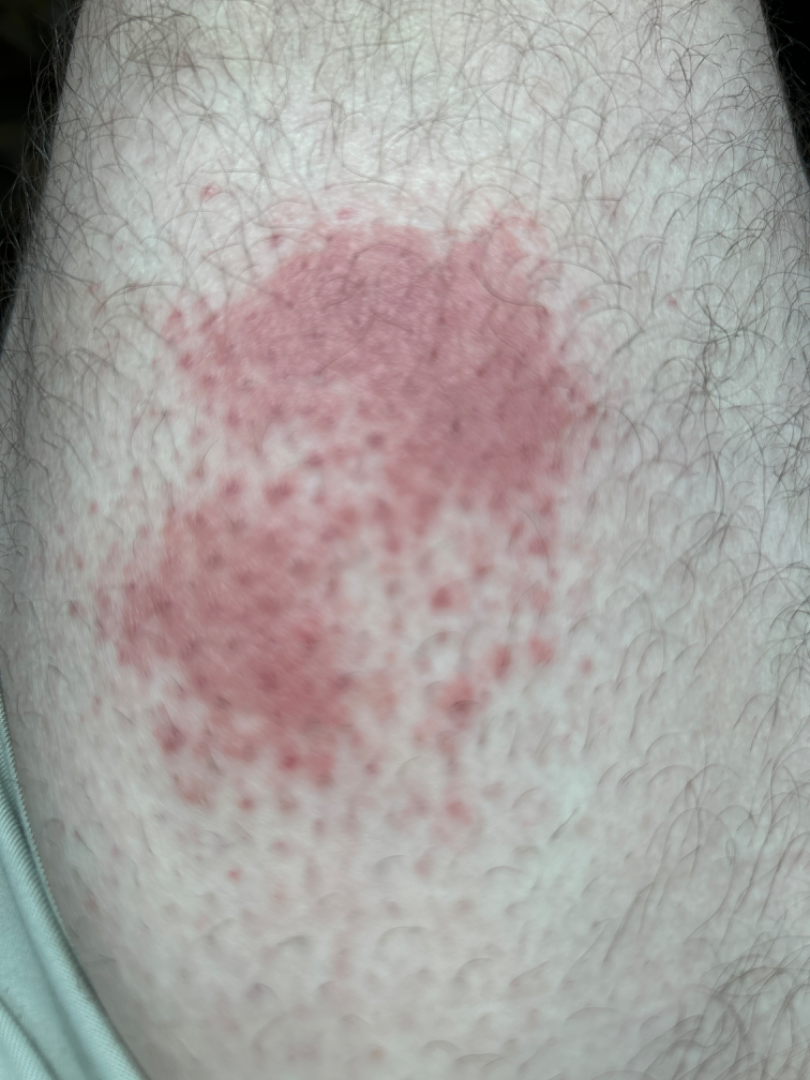Q: Could the case be diagnosed?
A: could not be assessed
Q: Who is the patient?
A: male, age 30–39
Q: What is the framing?
A: close-up
Q: Where on the body?
A: leg